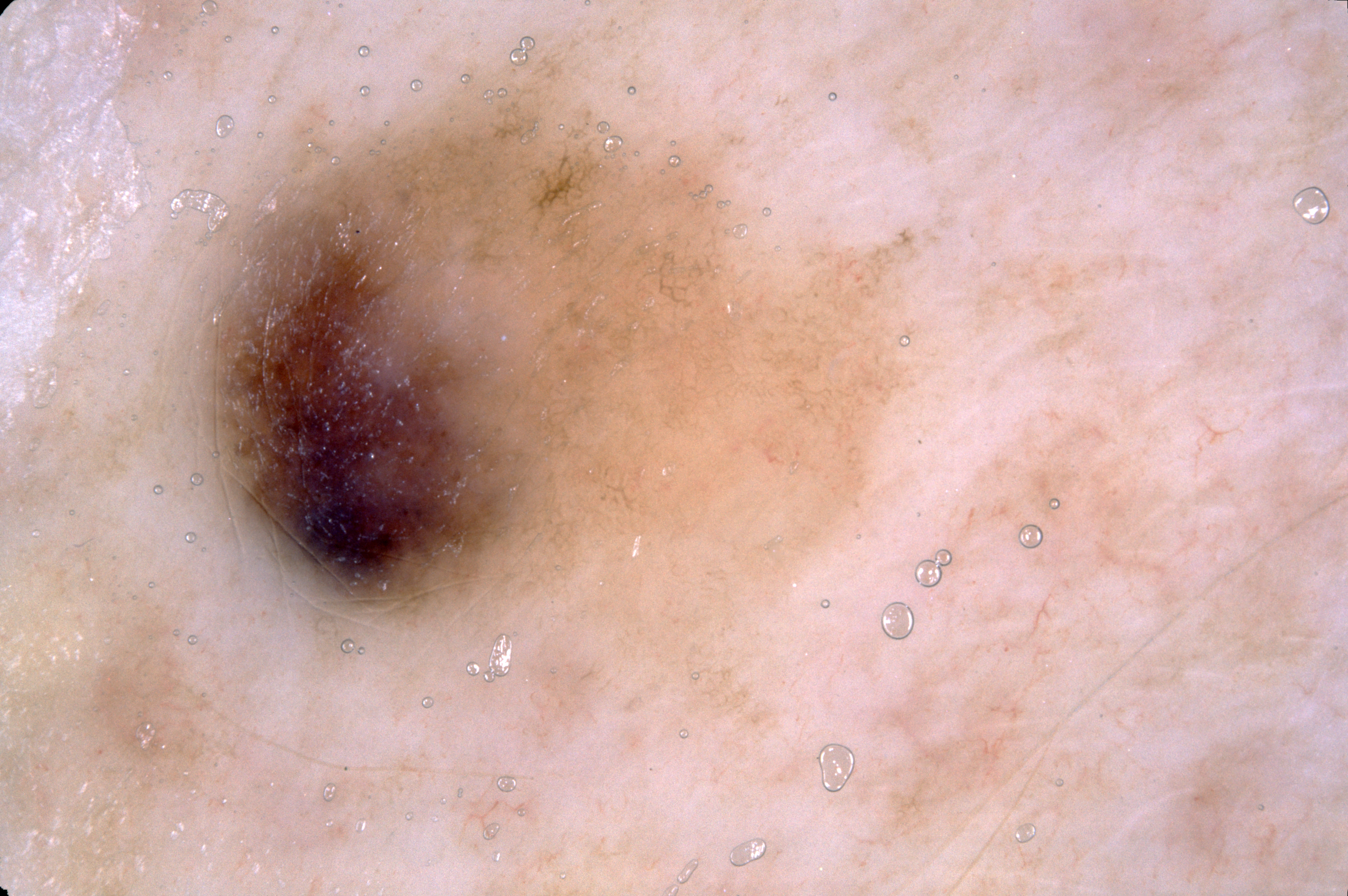Case summary:
• patient: female, about 50 years old
• image: dermatoscopic image of a skin lesion
• bounding box: x1=190, y1=63, x2=906, y2=630
• features: pigment network
• lesion extent: moderate
• diagnostic label: a melanocytic nevus, a benign skin lesion